On a questionnaire the patient reported no immunosuppression and no sunbed use. The patient describes having a moderate number of moles. Collected as part of a research study, without a referral diagnosis. The patient says their skin tans without first burning — 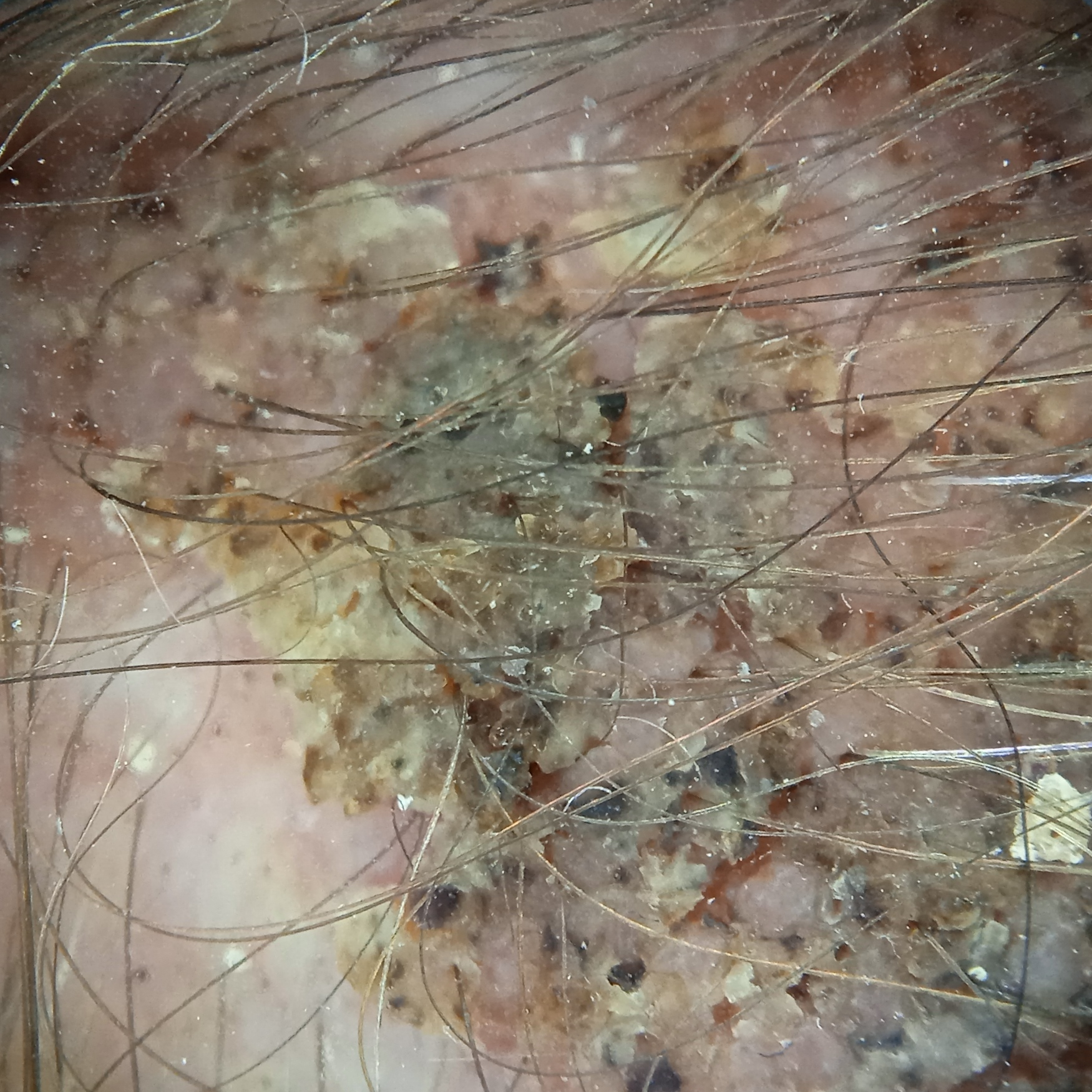location = the head | size = 19.2 mm | assessment = seborrheic keratosis (dermatologist consensus).